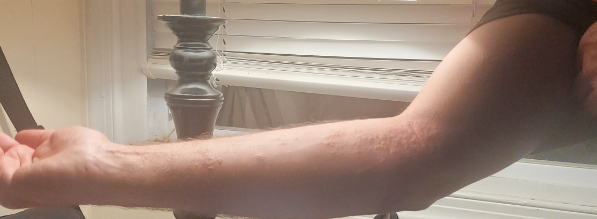skin tone = FST III; human graders estimated Monk skin tone scale 2
other reported symptoms = none reported
texture = raised or bumpy
patient describes the issue as = a rash
lesion symptoms = itching
body site = arm
image framing = at a distance
assessment = the differential includes Acute and chronic dermatitis and Allergic Contact Dermatitis, with no clear leading consideration